A dermoscopic close-up of a skin lesion, a male subject aged 68 to 72 — 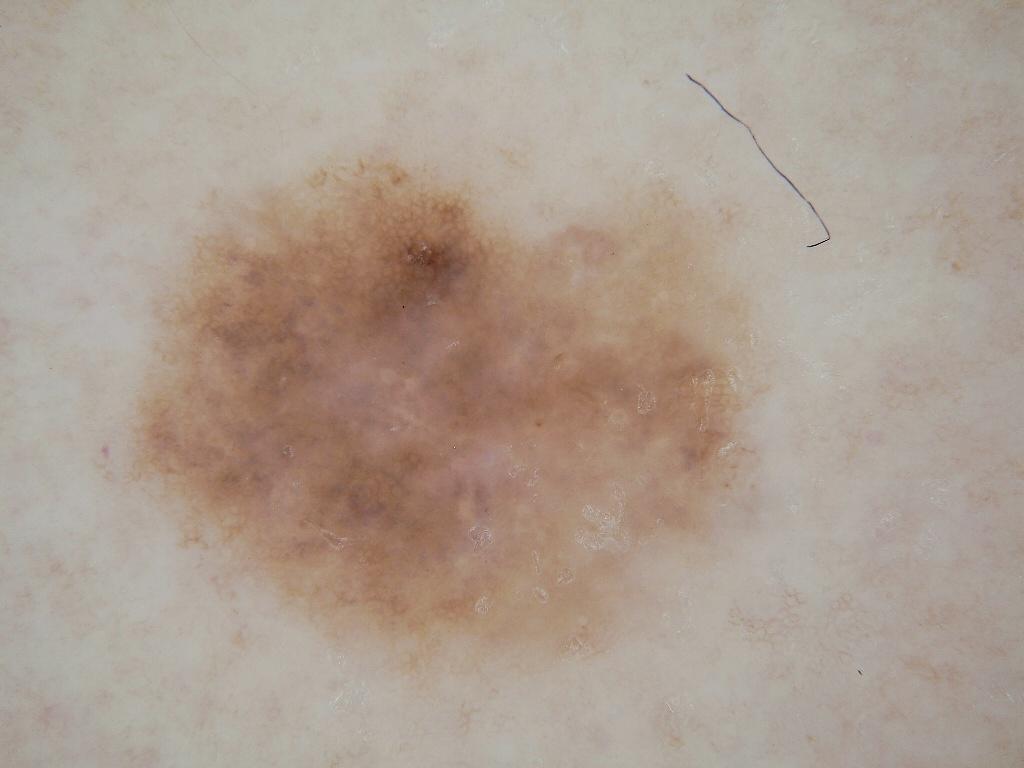The lesion covers approximately 32% of the dermoscopic field.
Dermoscopic examination shows pigment network, with no milia-like cysts, globules, streaks, or negative network.
In (x1, y1, x2, y2) order, the lesion occupies the region box(122, 146, 763, 687).
Consistent with a melanocytic nevus.